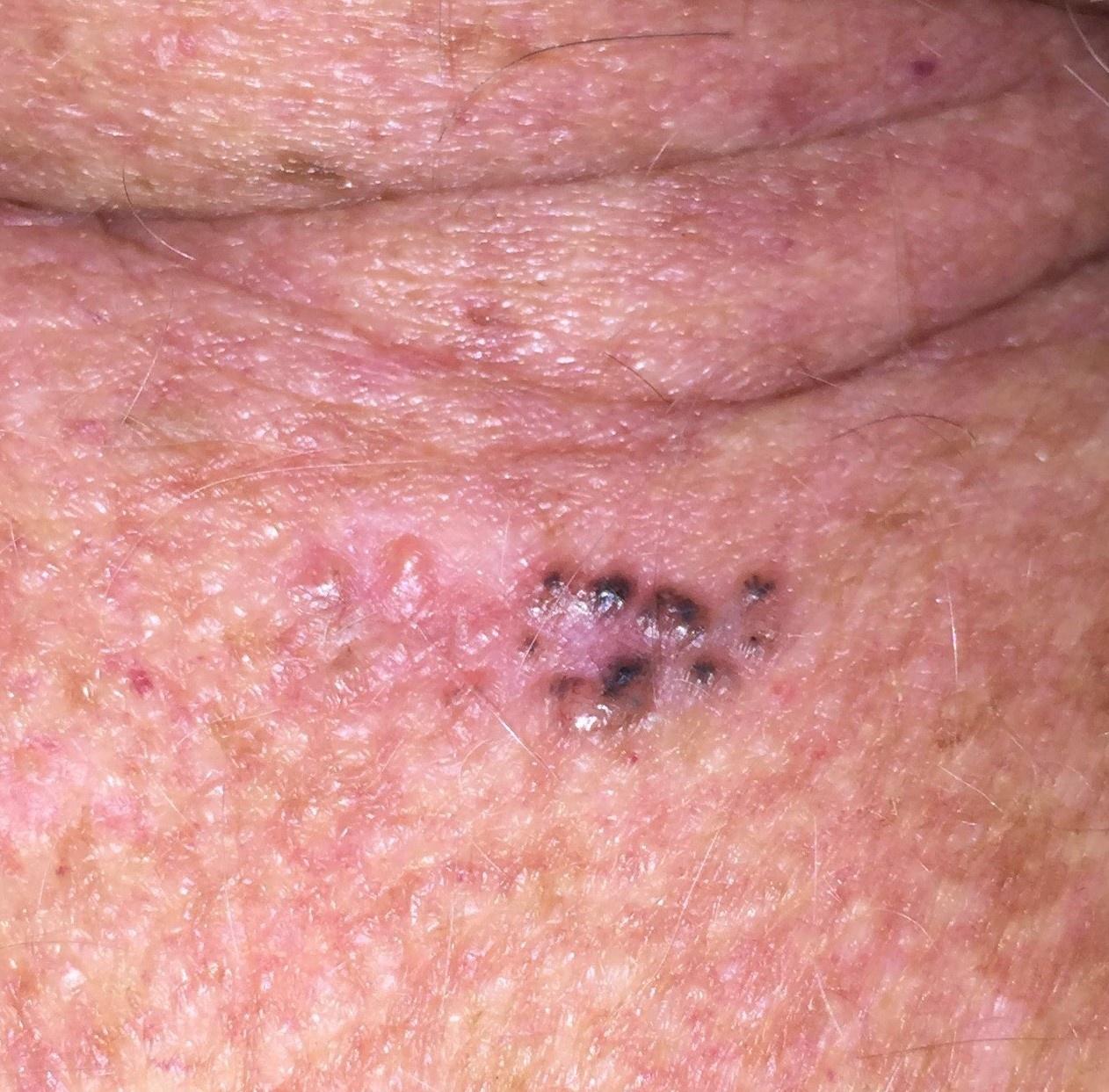{"patient": {"age_approx": 80, "sex": "male"}, "image": "clinical photo (overview)", "lesion_location": {"region": "the trunk", "detail": "the posterior trunk"}, "diagnosis": {"name": "Basal cell carcinoma", "malignancy": "malignant", "confirmation": "histopathology", "lineage": "adnexal"}}